A clinical photograph showing a skin lesion. The patient was assessed as Fitzpatrick skin type I. The chart notes alcohol use, prior skin cancer (patient or family), and no pesticide exposure:
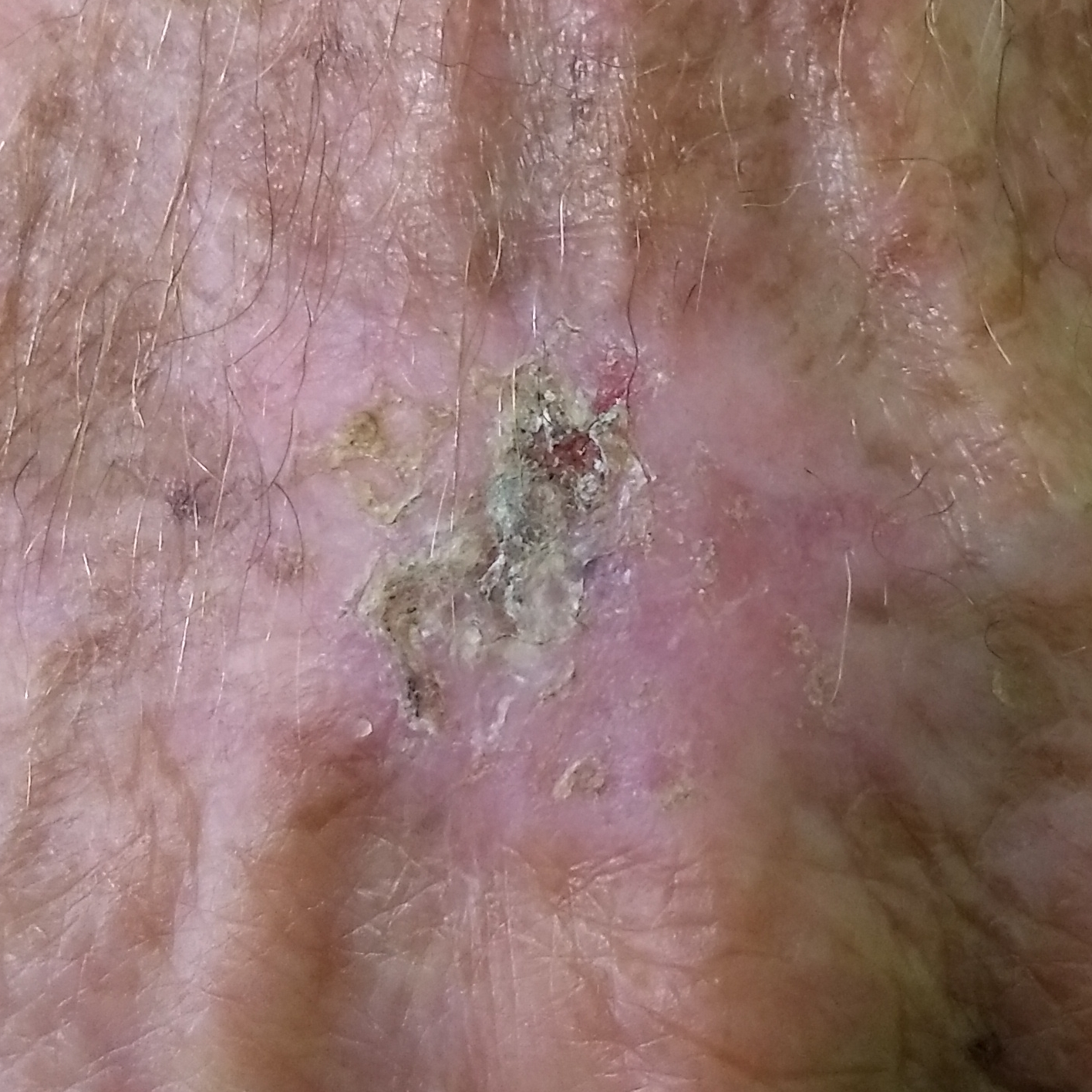The lesion is located on a hand. The lesion measures 12 × 10 mm. The patient reports that the lesion has grown, is elevated, itches, has changed, and has bled. The biopsy diagnosis was a malignant lesion — a basal cell carcinoma.